The patient is Fitzpatrick skin type II. An overview clinical photograph of a skin lesion. A male patient in their mid-40s — 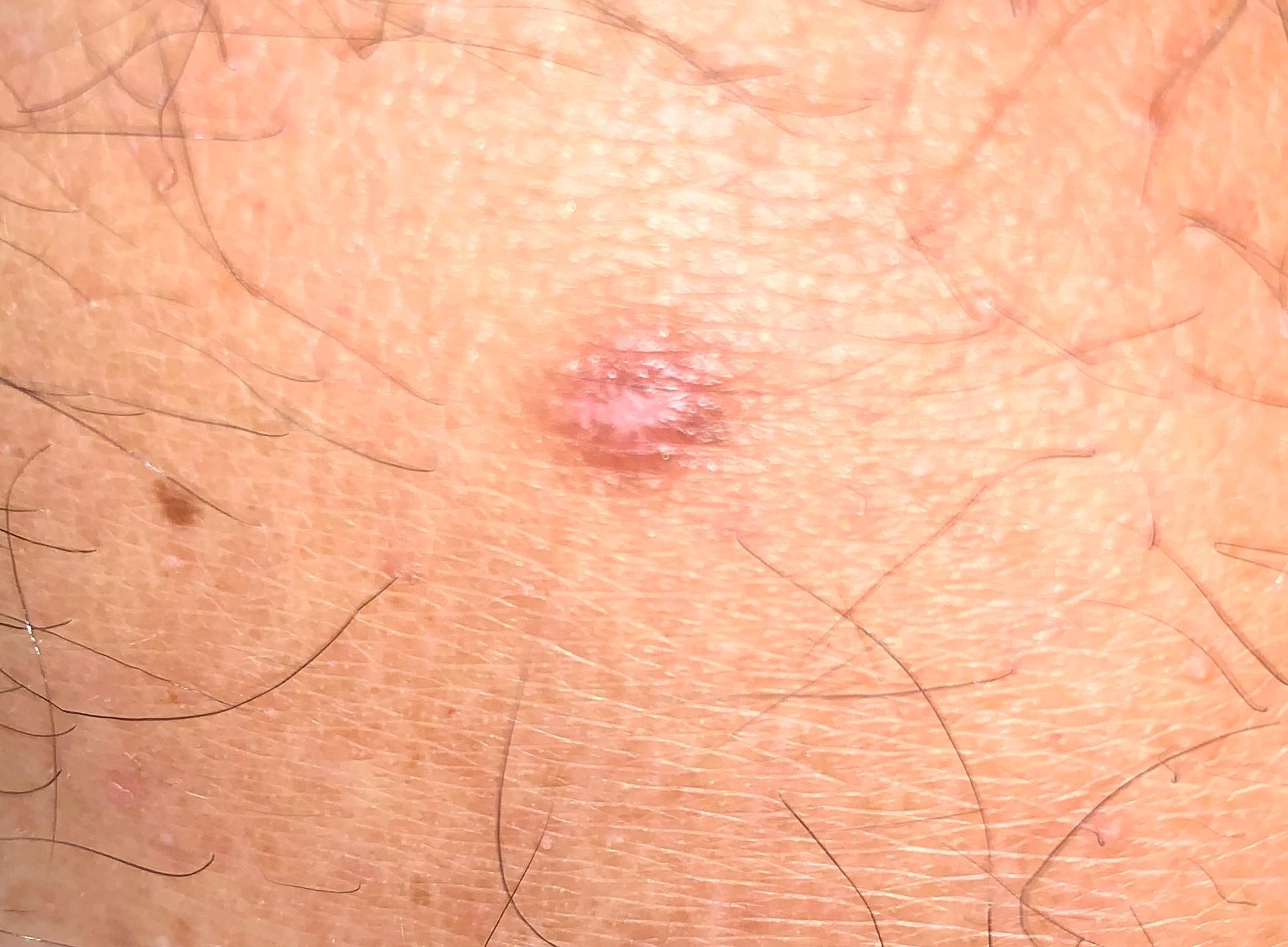impression: Dermatofibroma